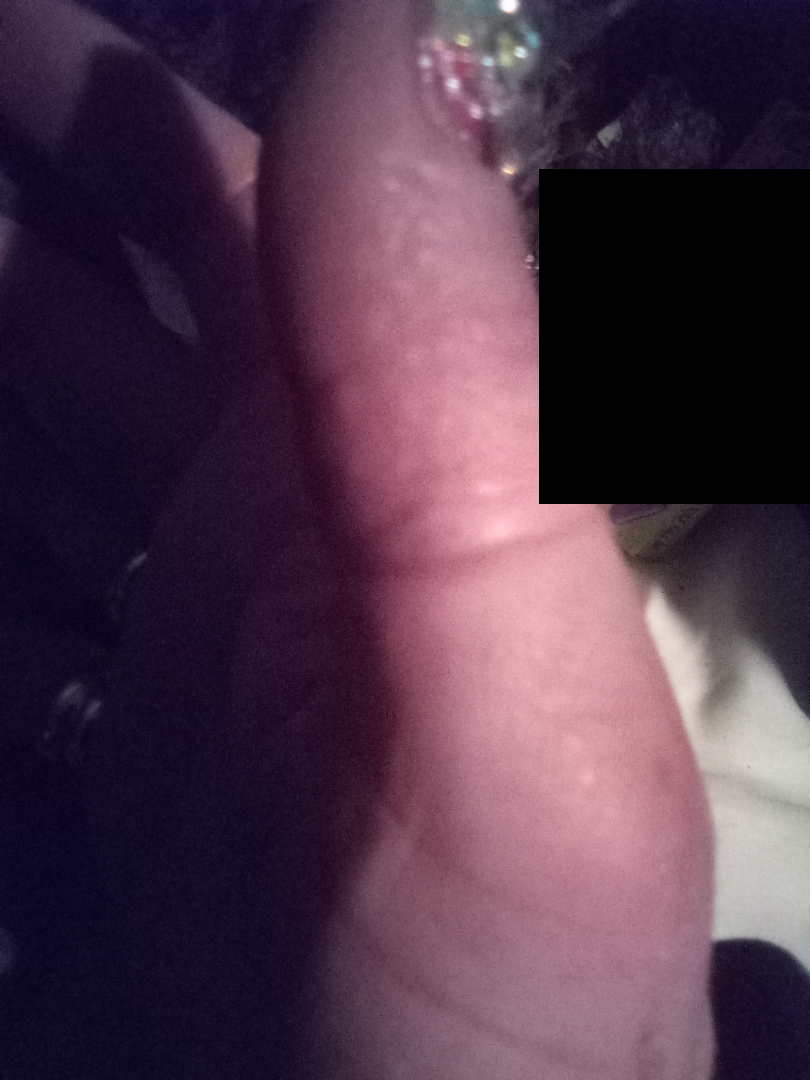assessment = ungradable on photographic review.